The contributor is a female aged 30–39 · the photo was captured at an angle:
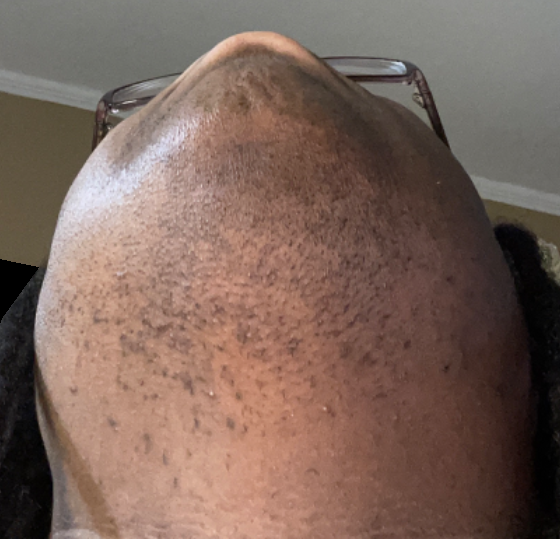dermatologist impression = most likely Post-Inflammatory hyperpigmentation; possibly Folliculitis; also on the differential is Scar Condition